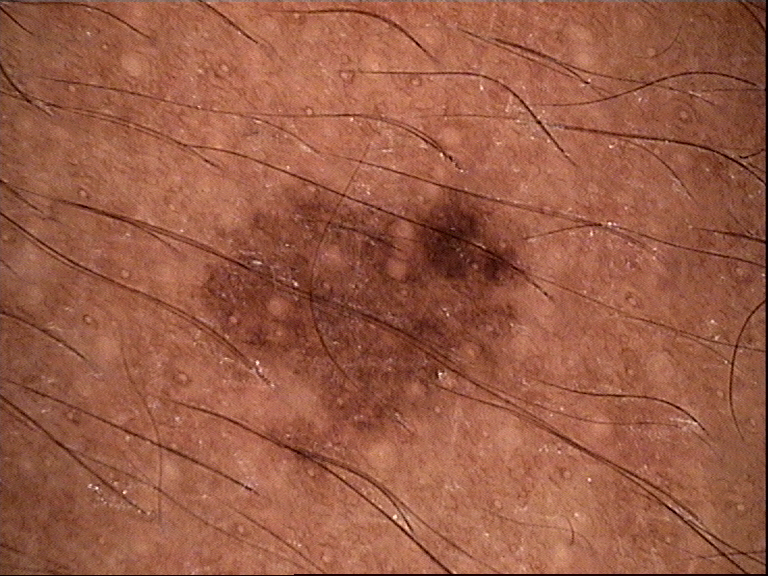Dermoscopy of a skin lesion. Consistent with a dysplastic junctional nevus.